The photograph is a close-up of the affected area:
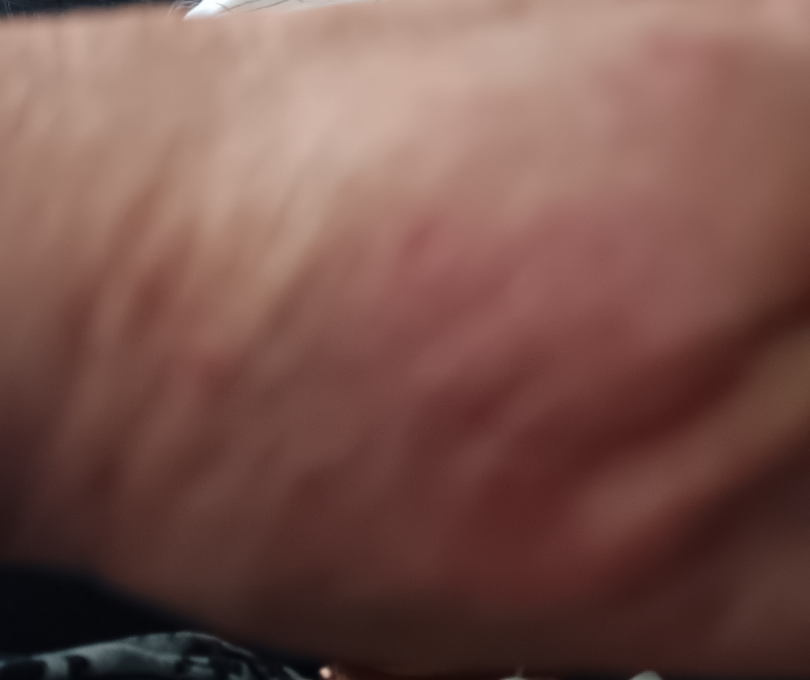The reviewing dermatologist was unable to assign a differential diagnosis from the image.